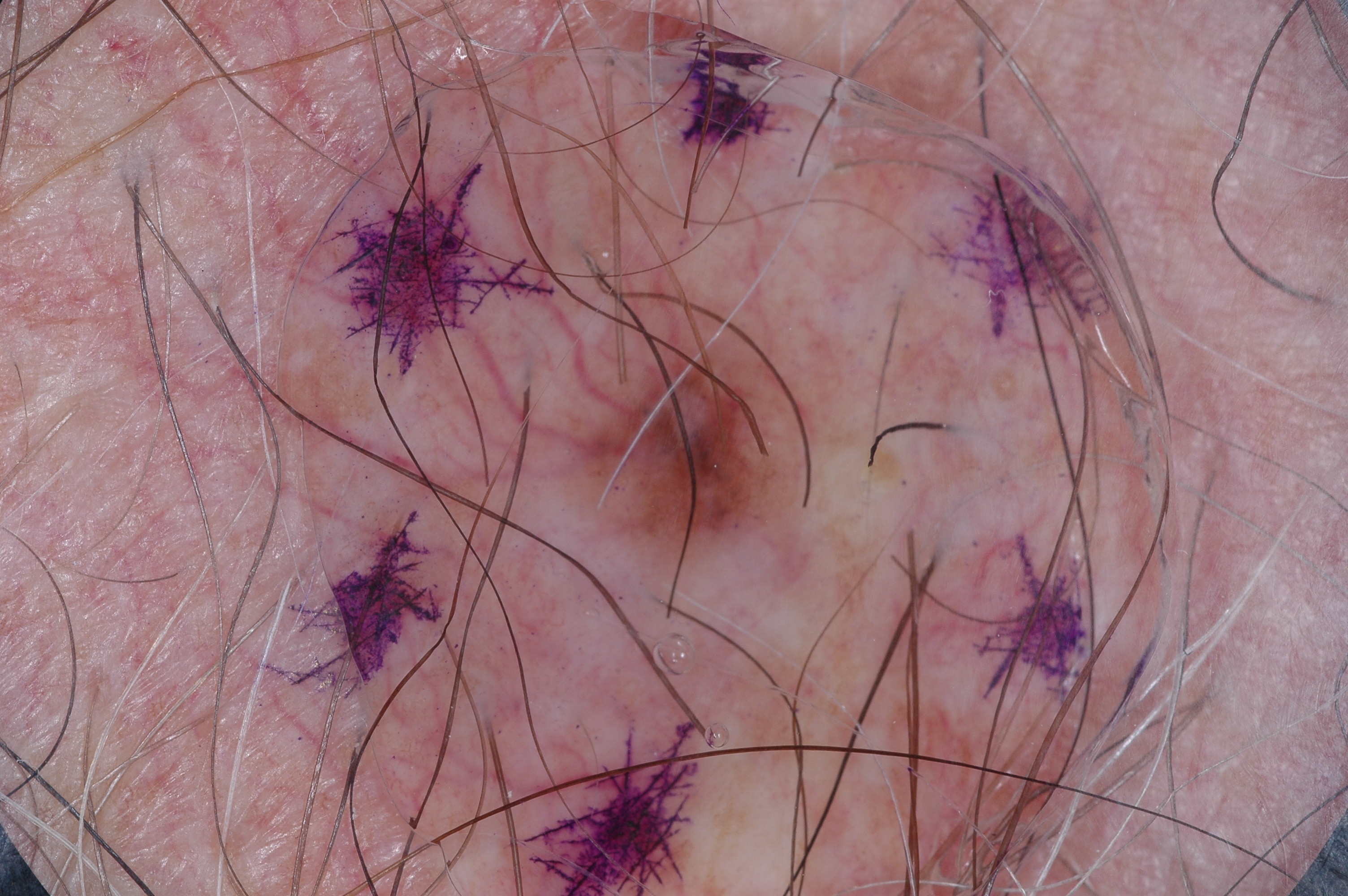image:
  modality: dermoscopy
lesion_extent:
  approx_field_fraction_pct: 4
dermoscopic_features:
  present:
    - pigment network
  absent:
    - milia-like cysts
    - negative network
    - streaks
lesion_location:
  bbox_xyxy:
    - 545
    - 308
    - 814
    - 573
diagnosis:
  name: melanocytic nevus
  malignancy: benign
  lineage: melanocytic
  provenance: clinical